Referred with a clinical suspicion of basal cell carcinoma — 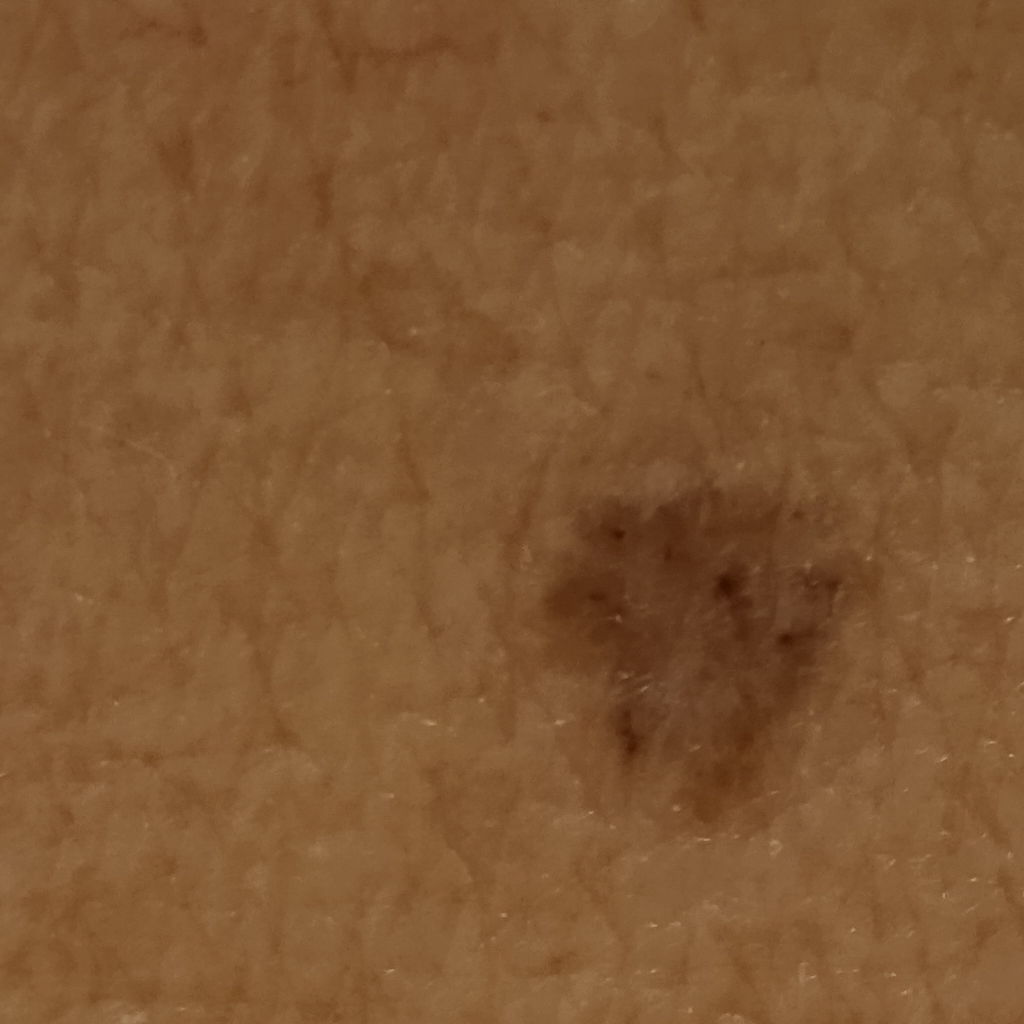Findings:
Located on the torso. The lesion measures approximately 7.2 mm.
Assessment:
The consensus diagnosis for this lesion was a basal cell carcinoma.